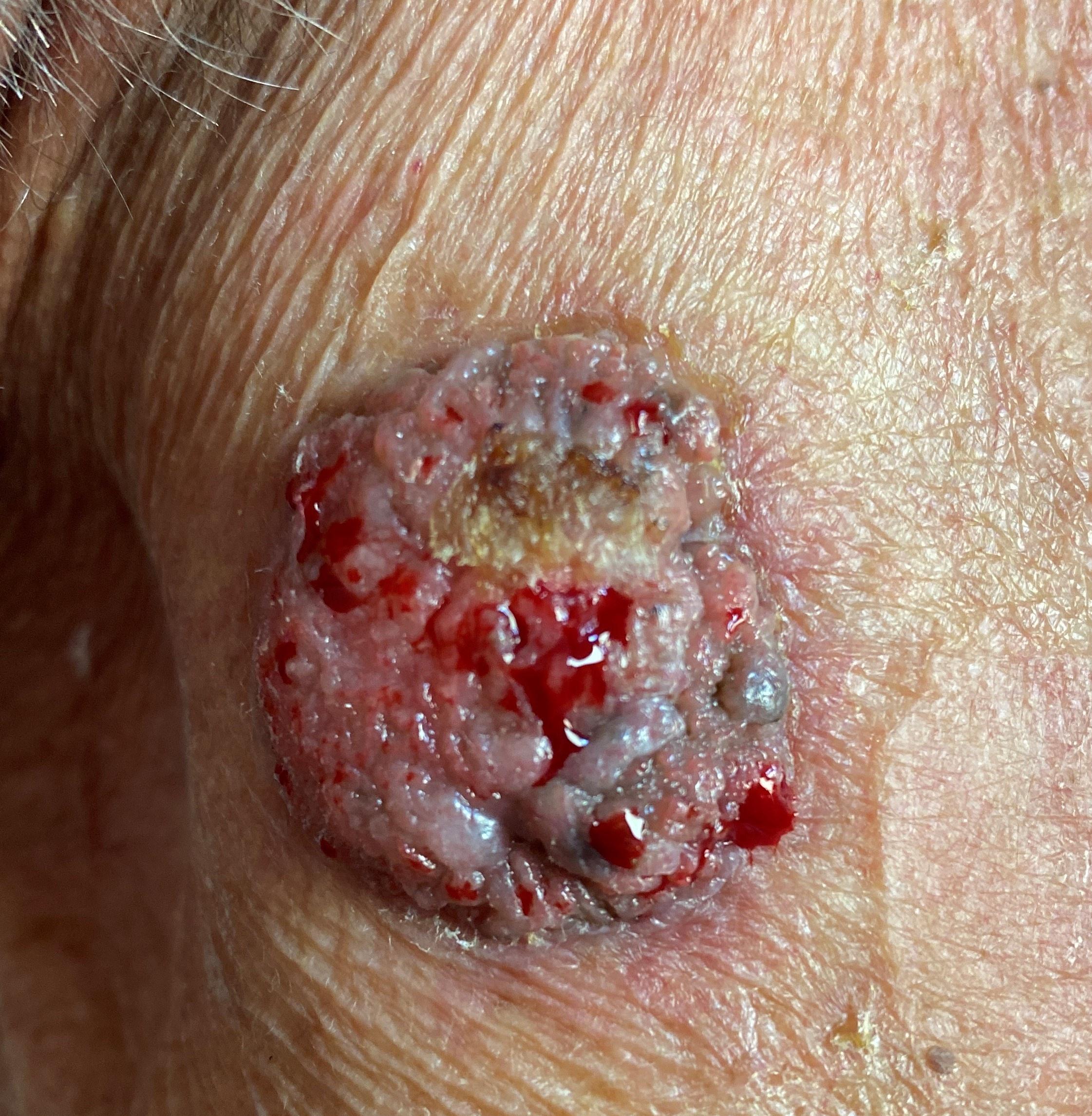Q: What Fitzpatrick skin type was recorded?
A: II
Q: Who is the patient?
A: male, roughly 80 years of age
Q: What kind of image is this?
A: clinical overview photograph
Q: What is the anatomic site?
A: the trunk
Q: What did the workup show?
A: Basal cell carcinoma (biopsy-proven)